A dermoscopic photograph of a skin lesion:
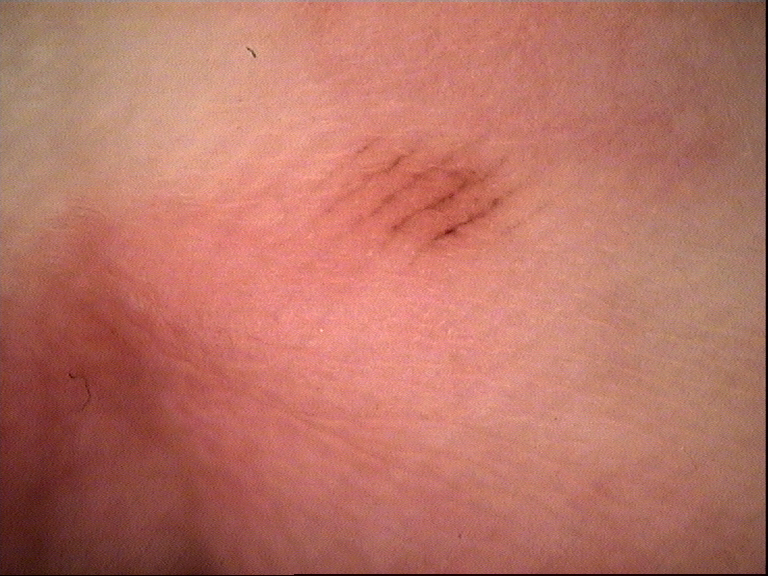Findings:
• label — acral junctional nevus (expert consensus)